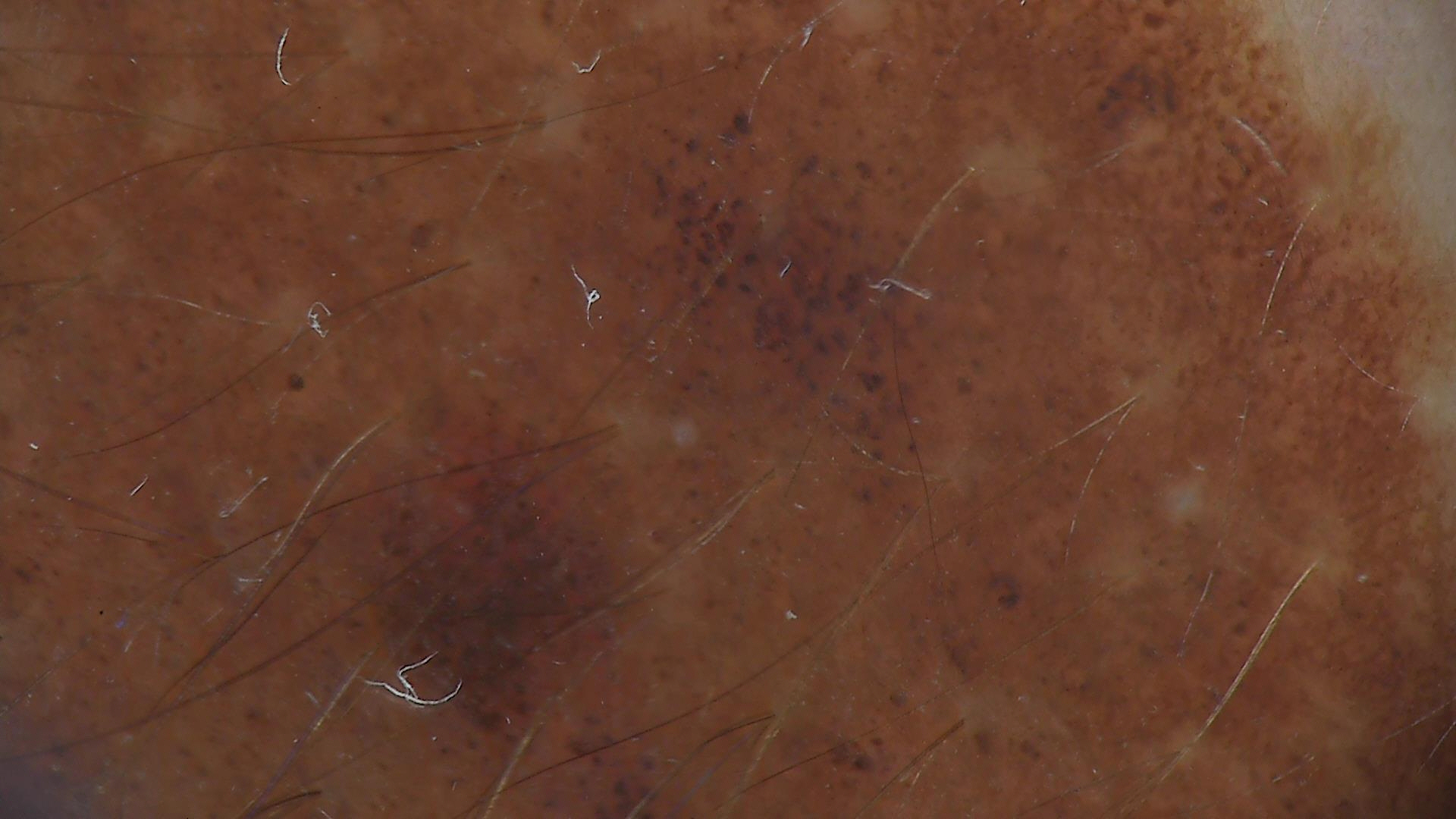Findings:
A dermatoscopic image of a skin lesion. The architecture is that of a banal lesion.
Impression:
Classified as a congenital junctional nevus.